This is a close-up image:
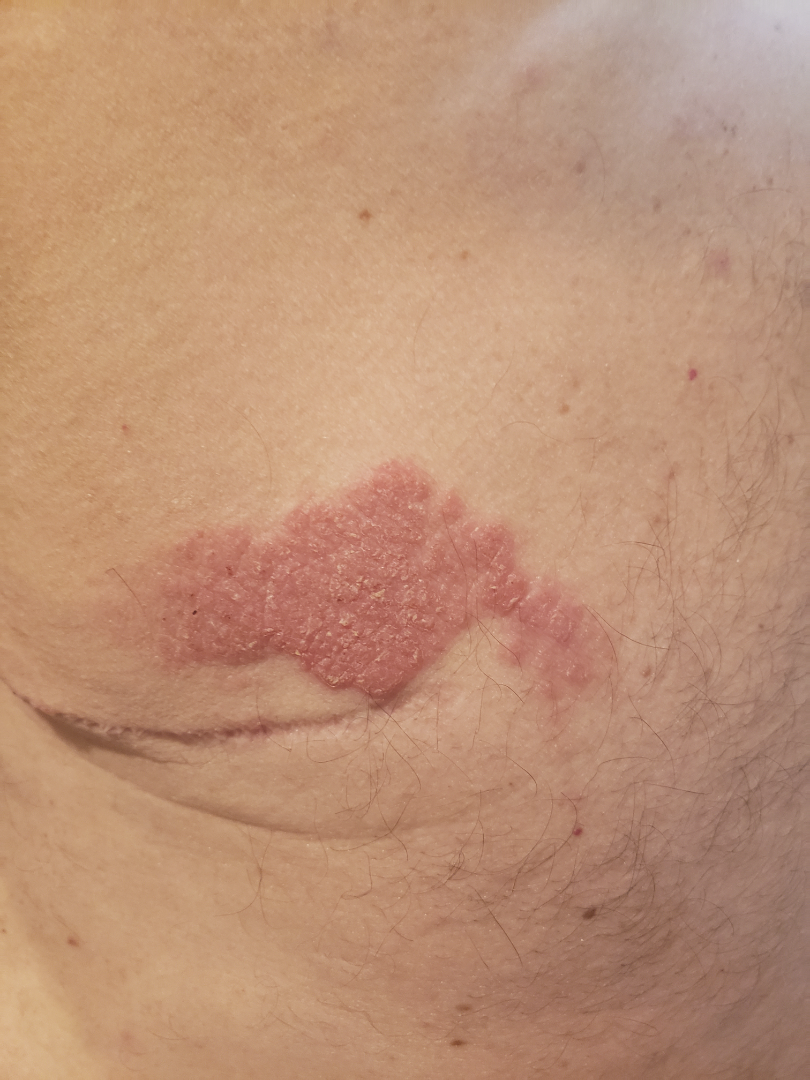Impression:
On remote review of the image, Psoriasis (weight 0.67); Eczema (weight 0.33).